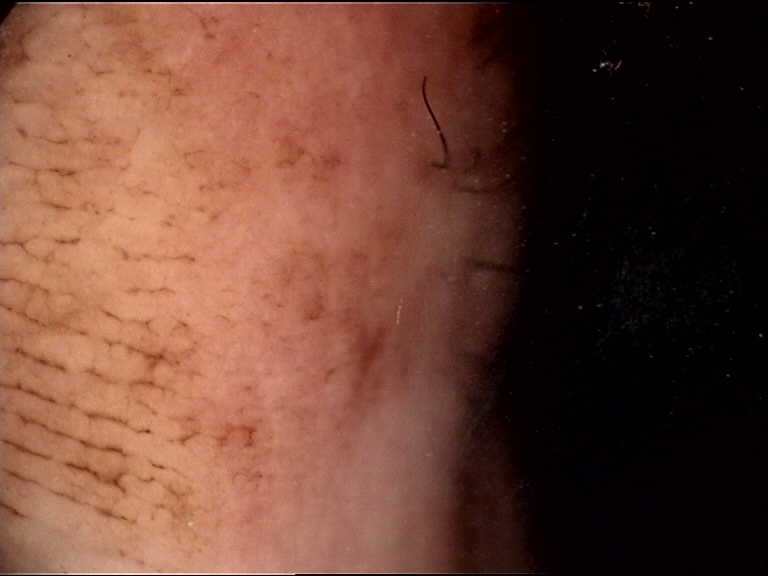Summary: A dermatoscopic image of a skin lesion. Impression: Diagnosed as an acral junctional nevus.